The photo was captured at a distance; the contributor is a female aged 18–29:
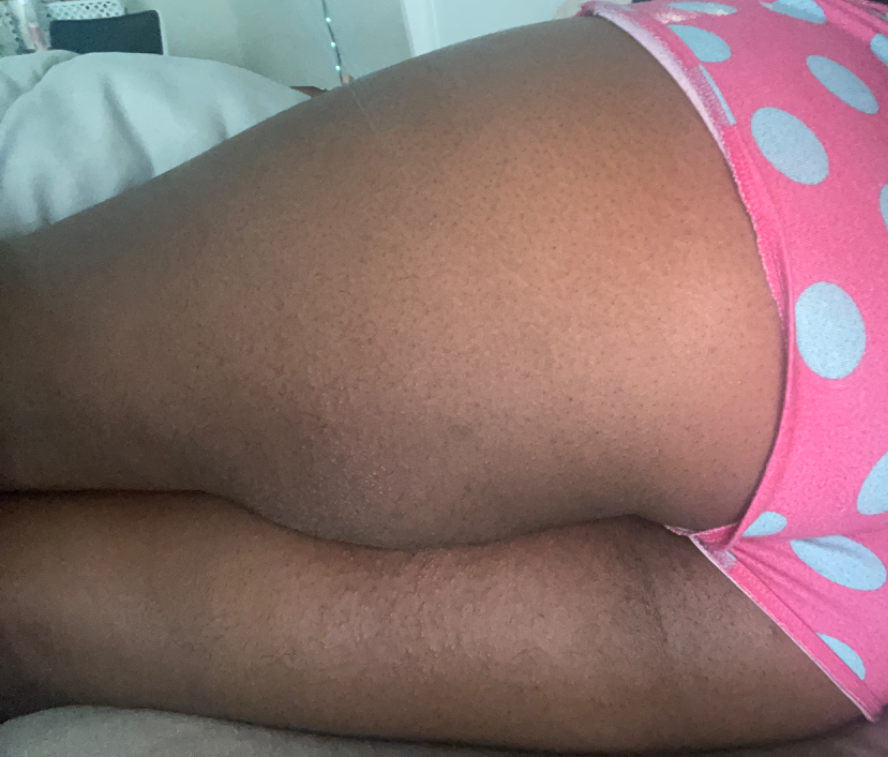Findings:
– dermatologist impression · favoring Eczema; also raised was Folliculitis